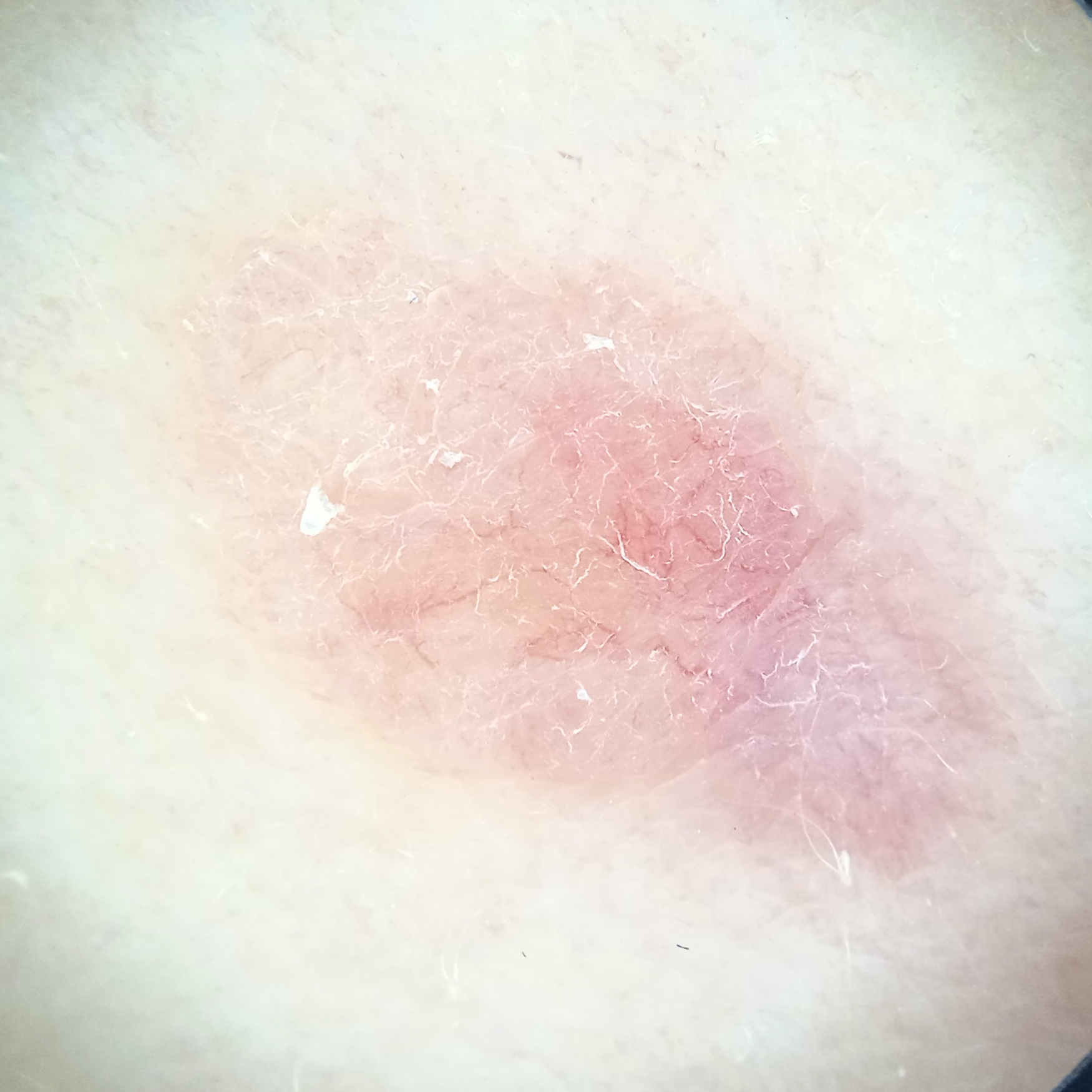On biopsy, the diagnosis was a basal cell carcinoma, following excision, with a measured thickness of 1.1 mm.